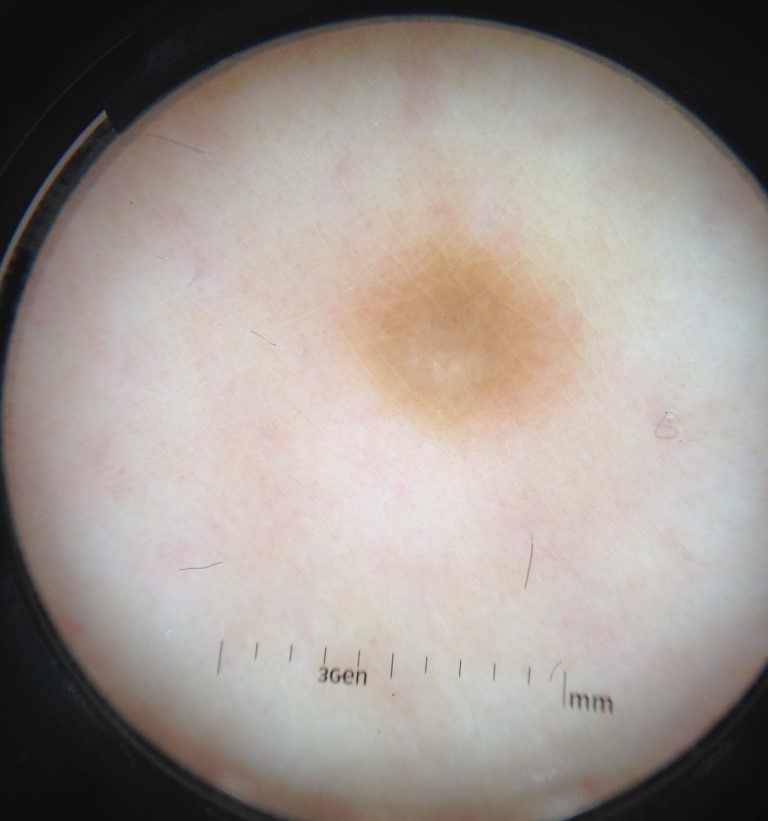Case:
– image: dermoscopy
– diagnostic label: dermatofibroma (expert consensus)